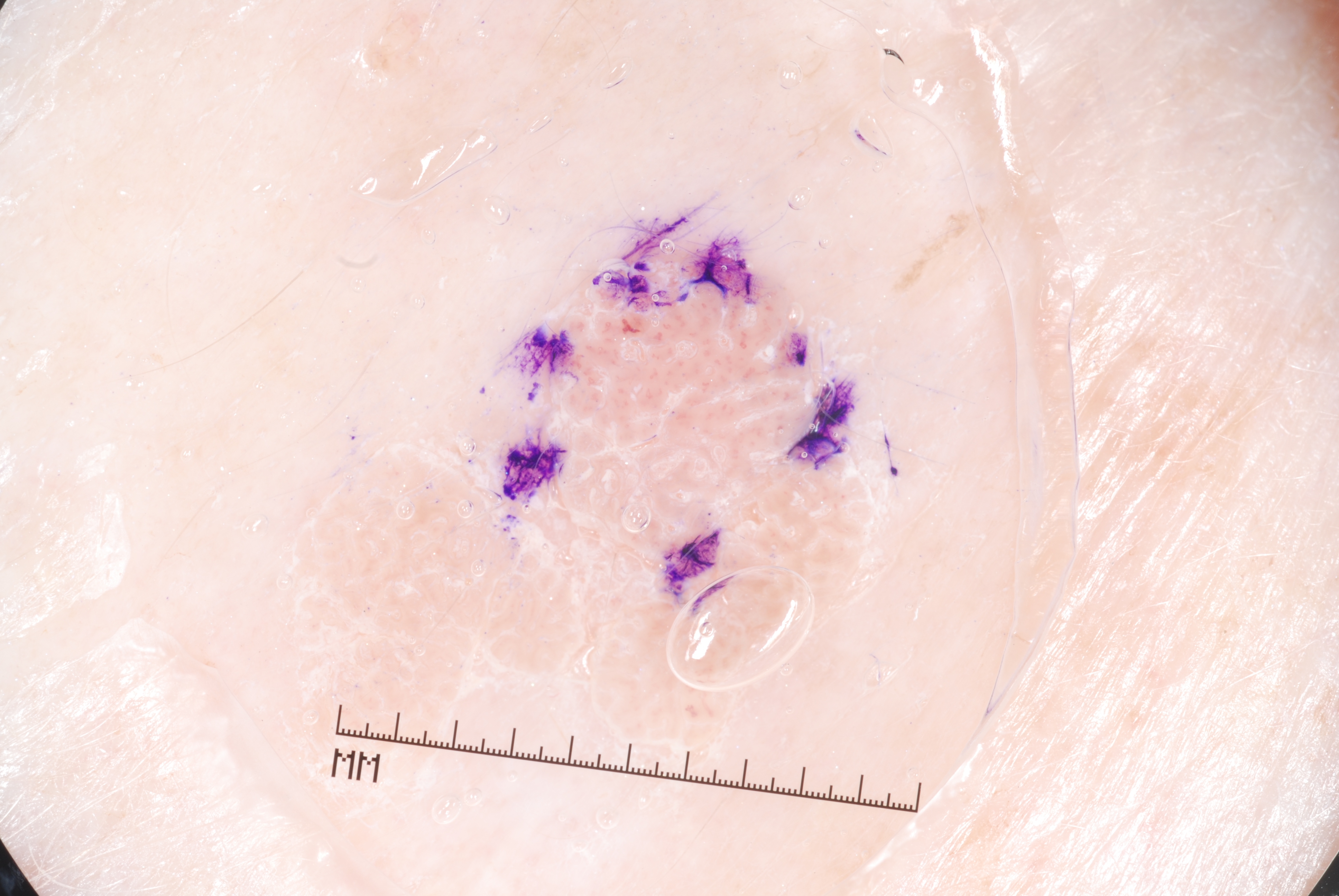Q: Patient demographics?
A: female, roughly 70 years of age
Q: What kind of image is this?
A: dermoscopy
Q: What is the lesion's bounding box?
A: 275/222/914/823
Q: What does dermoscopy show?
A: milia-like cysts; absent: pigment network, streaks, and negative network
Q: What is this lesion?
A: a seborrheic keratosis, a lesion of keratinocytic origin